The photograph was taken at an angle, the contributor notes the lesion is flat, the lesion involves the arm, no associated systemic symptoms reported, present for about one day: 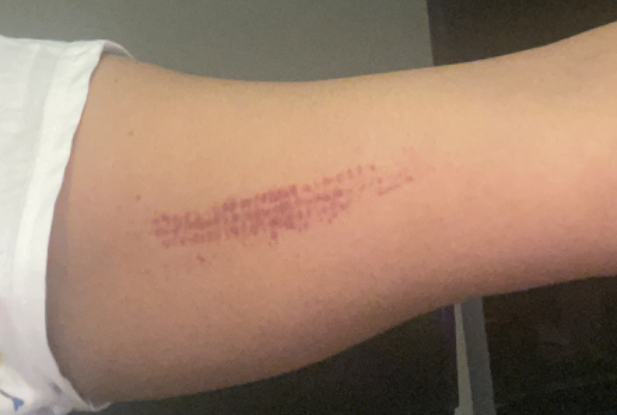differential:
  ecchymoses: 1.0